Reported duration is about one day, self-categorized by the patient as a rash, the photograph is a close-up of the affected area, the back of the torso is involved — 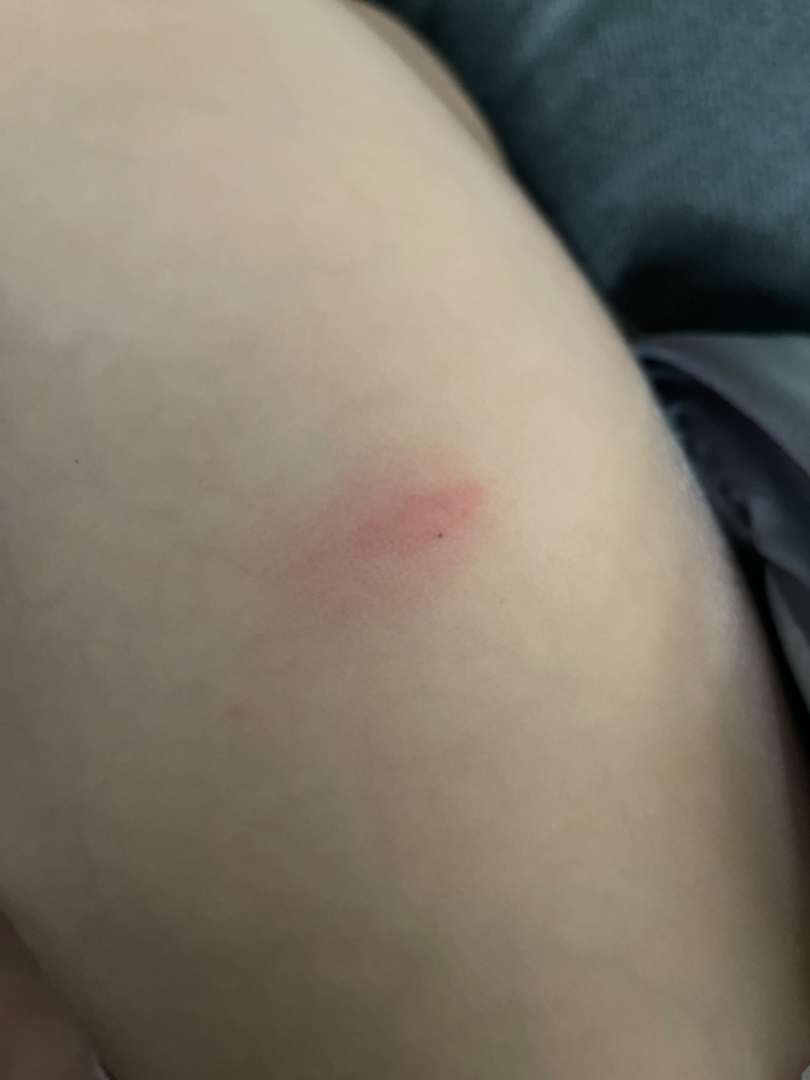Findings:
The dermatologist could not determine a likely condition from the photograph alone.